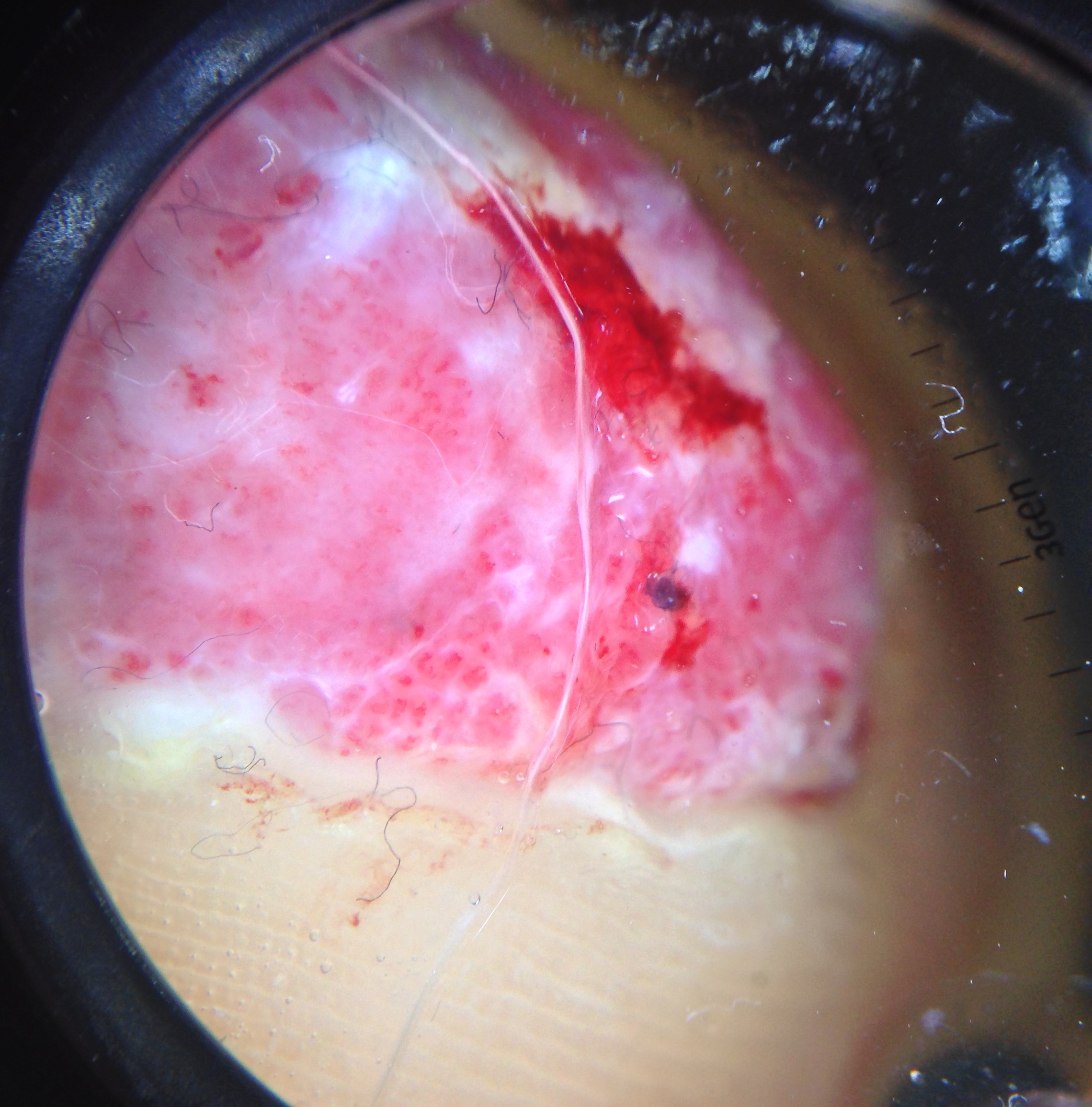image: dermatoscopy; diagnosis: acral nodular melanoma (biopsy-proven).